Self-categorized by the patient as a rash. Female subject, age 18–29. The leg and arm are involved. Texture is reported as raised or bumpy. An image taken at a distance. The lesion is associated with enlargement, bothersome appearance and itching. The patient notes the condition has been present for about one day:
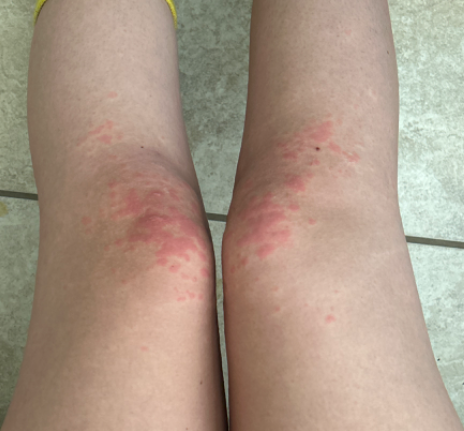Q: What is the differential diagnosis?
A: Viral Exanthem (1.00)